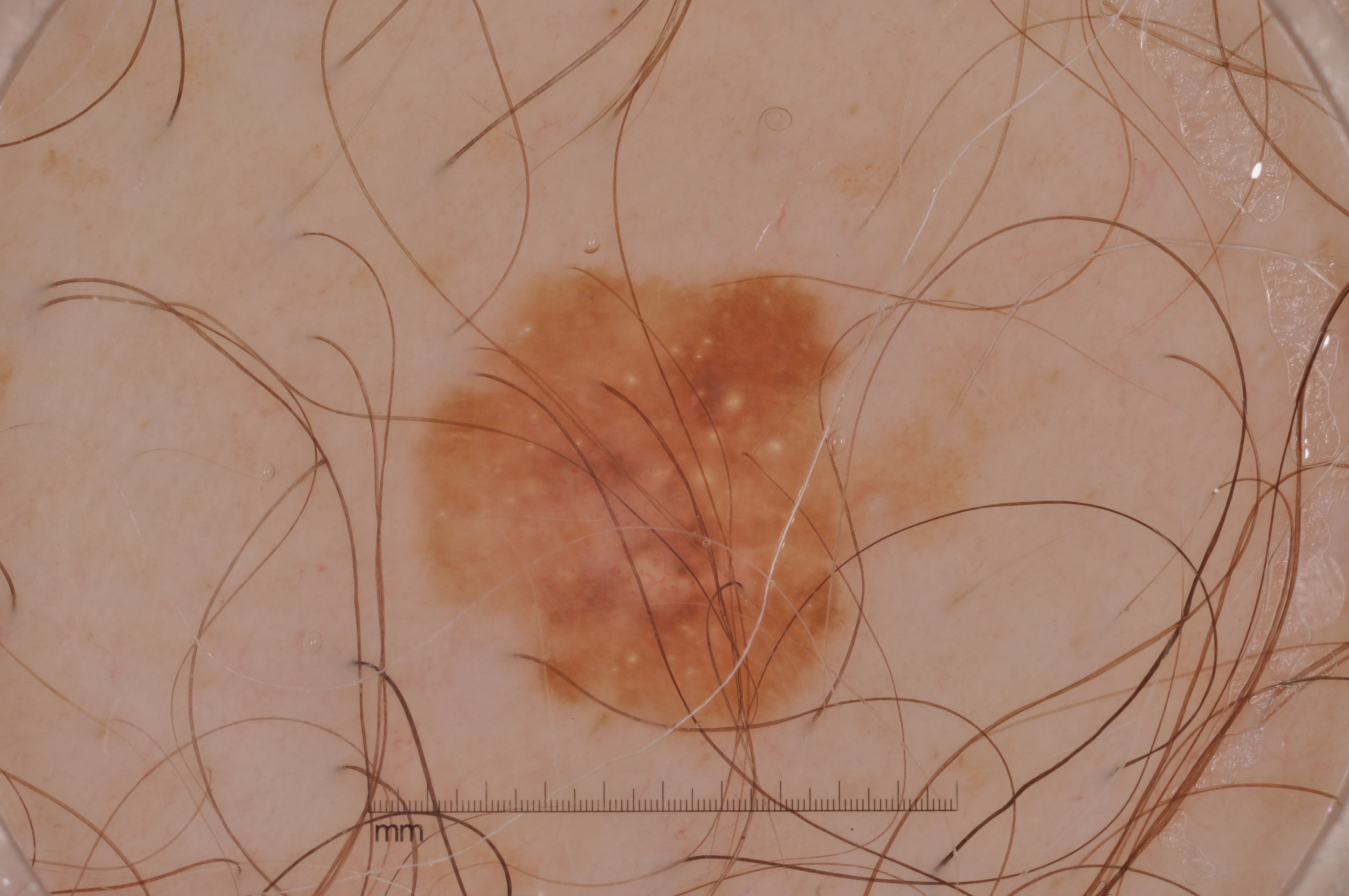Findings:
A male subject, aged around 65. A skin lesion imaged with a dermatoscope. Dermoscopically, the lesion shows milia-like cysts. The lesion is located at (422, 266, 927, 742).
Assessment:
Diagnosed as a seborrheic keratosis.